Dermoscopy of a skin lesion.
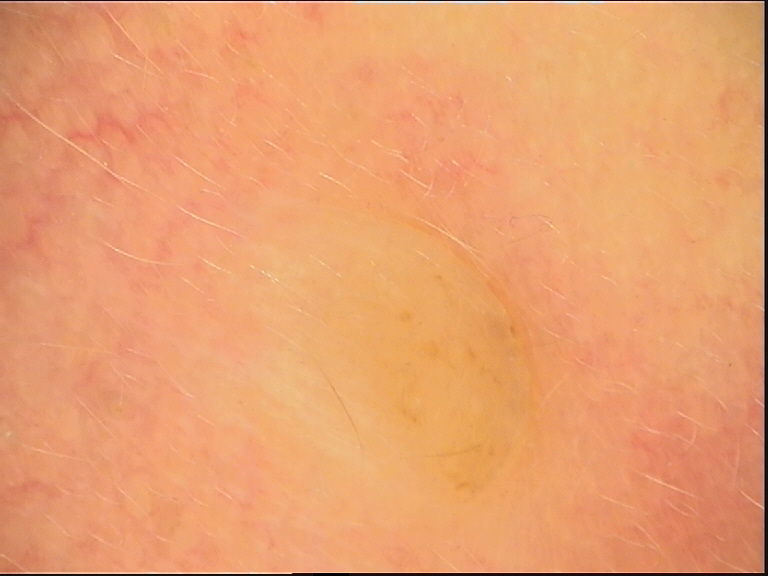The architecture is that of a banal lesion. Labeled as a dermal nevus.